A male patient, aged approximately 30 · a dermoscopic view of a skin lesion:
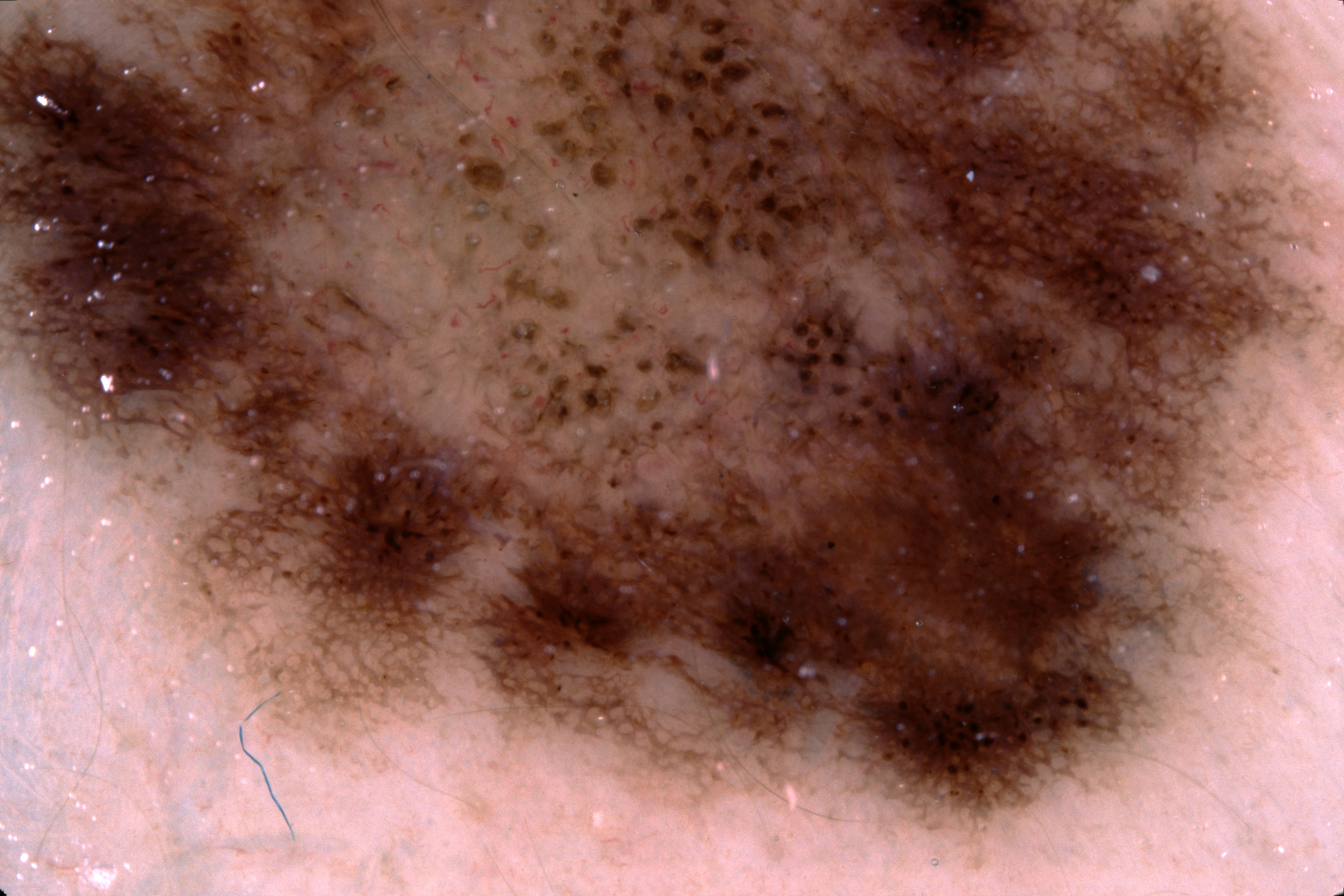Q: What is the lesion's bounding box?
A: spans the dermoscopic field
Q: What does dermoscopy show?
A: pigment network; absent: streaks, negative network, and milia-like cysts
Q: What did the assessment conclude?
A: a melanocytic nevus, a benign skin lesion